A dermatoscopic image of a skin lesion; a female subject aged 63-67:
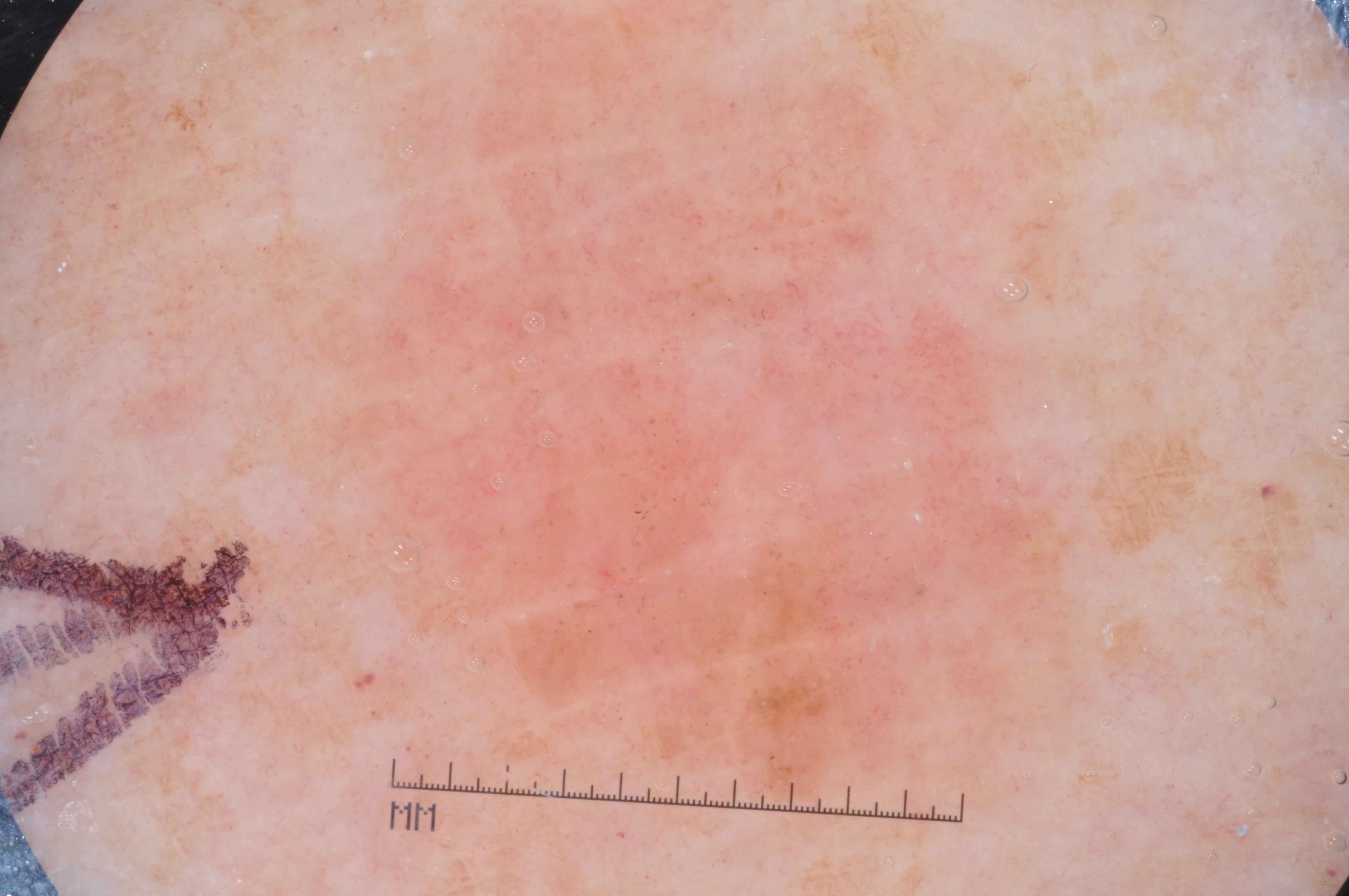Case summary: Lesion location: left=271, top=12, right=1091, bottom=826. Dermoscopically, the lesion shows milia-like cysts. The lesion occupies roughly 43% of the field. Diagnosis: Histopathologically confirmed as a melanoma, a malignant skin lesion.